Dermoscopy of a skin lesion.
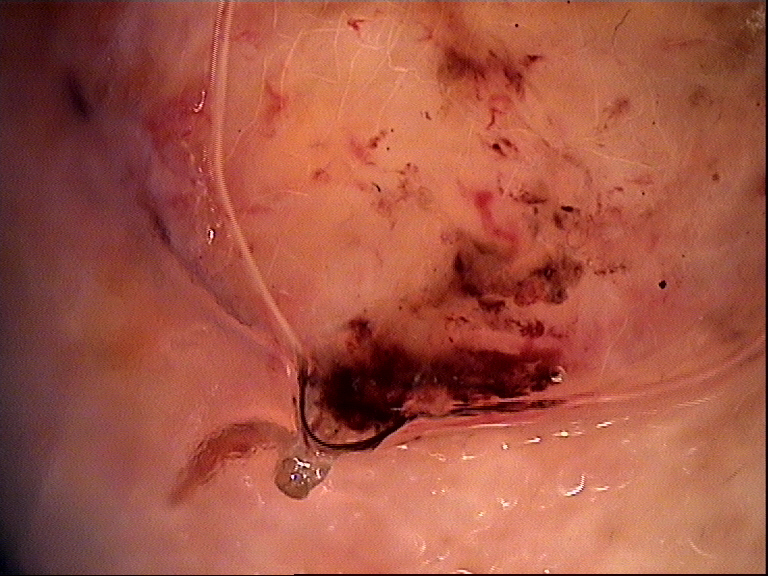Histopathologically confirmed as a keratinocytic, malignant lesion — a basal cell carcinoma.